This is a close-up image; the affected area is the arm.
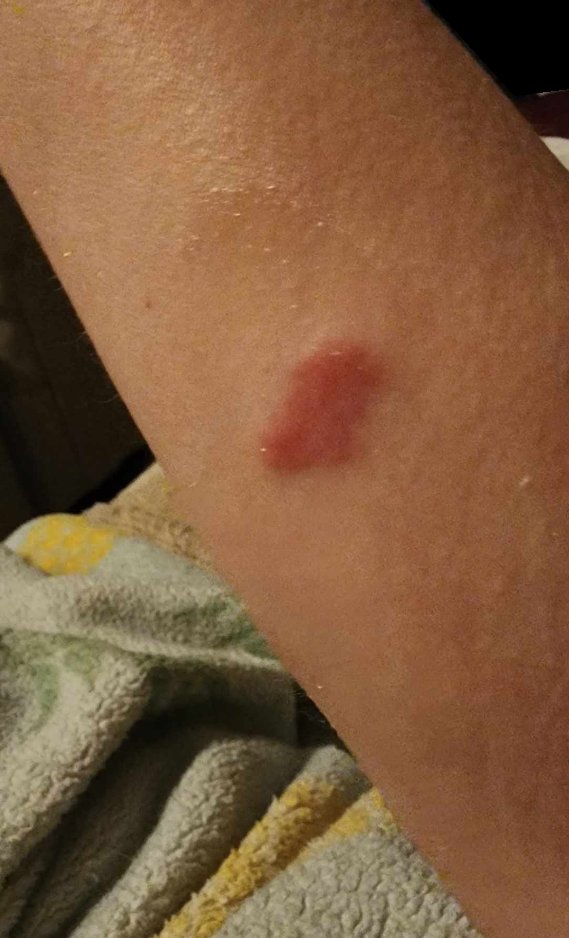differential diagnosis=Jessner lymphocytic infiltrate (54%); Leukemia cutis (23%); Cutaneous sarcoidosis (23%).